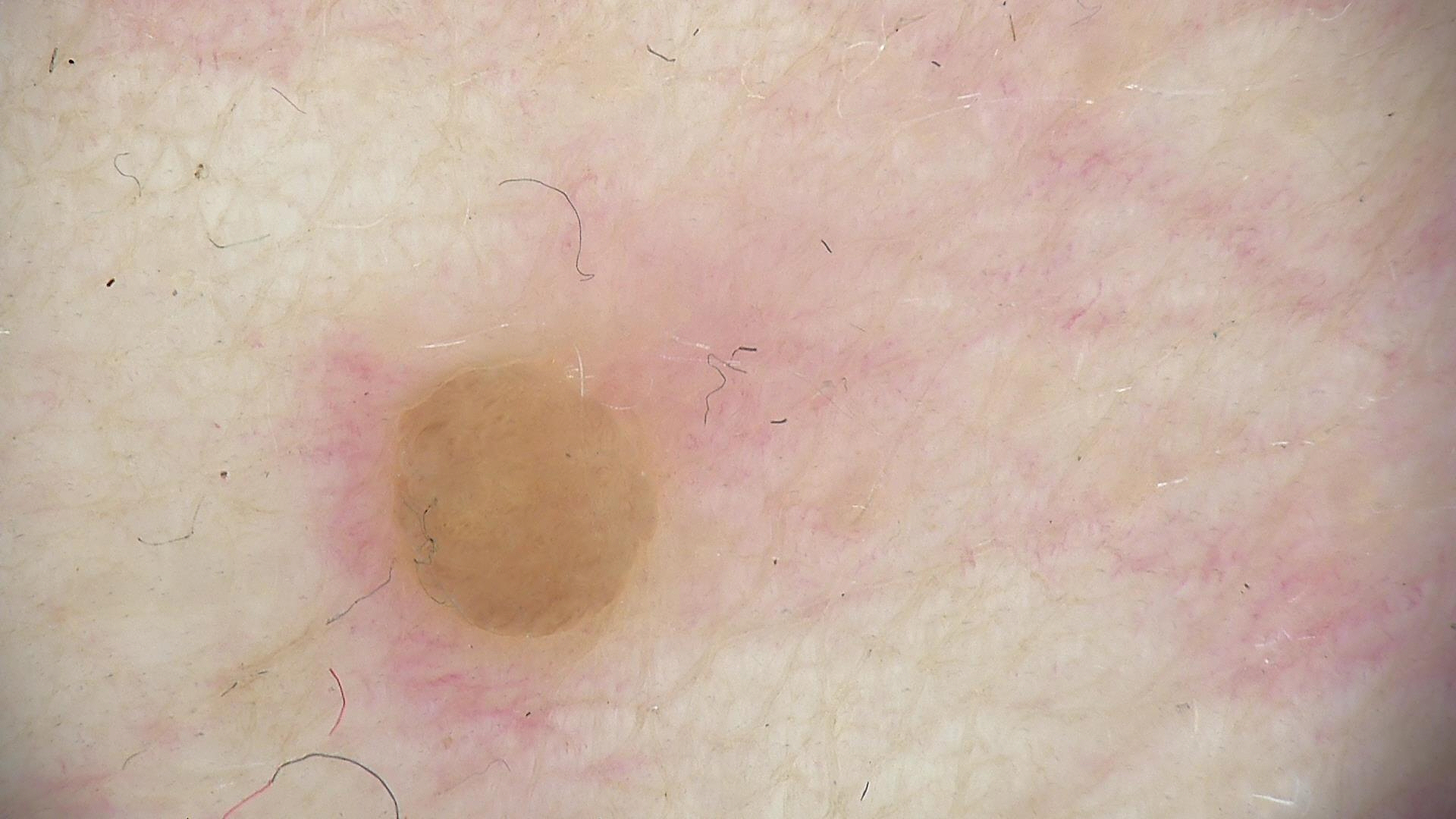image type = dermoscopy | category = banal | diagnosis = dermal nevus (expert consensus).